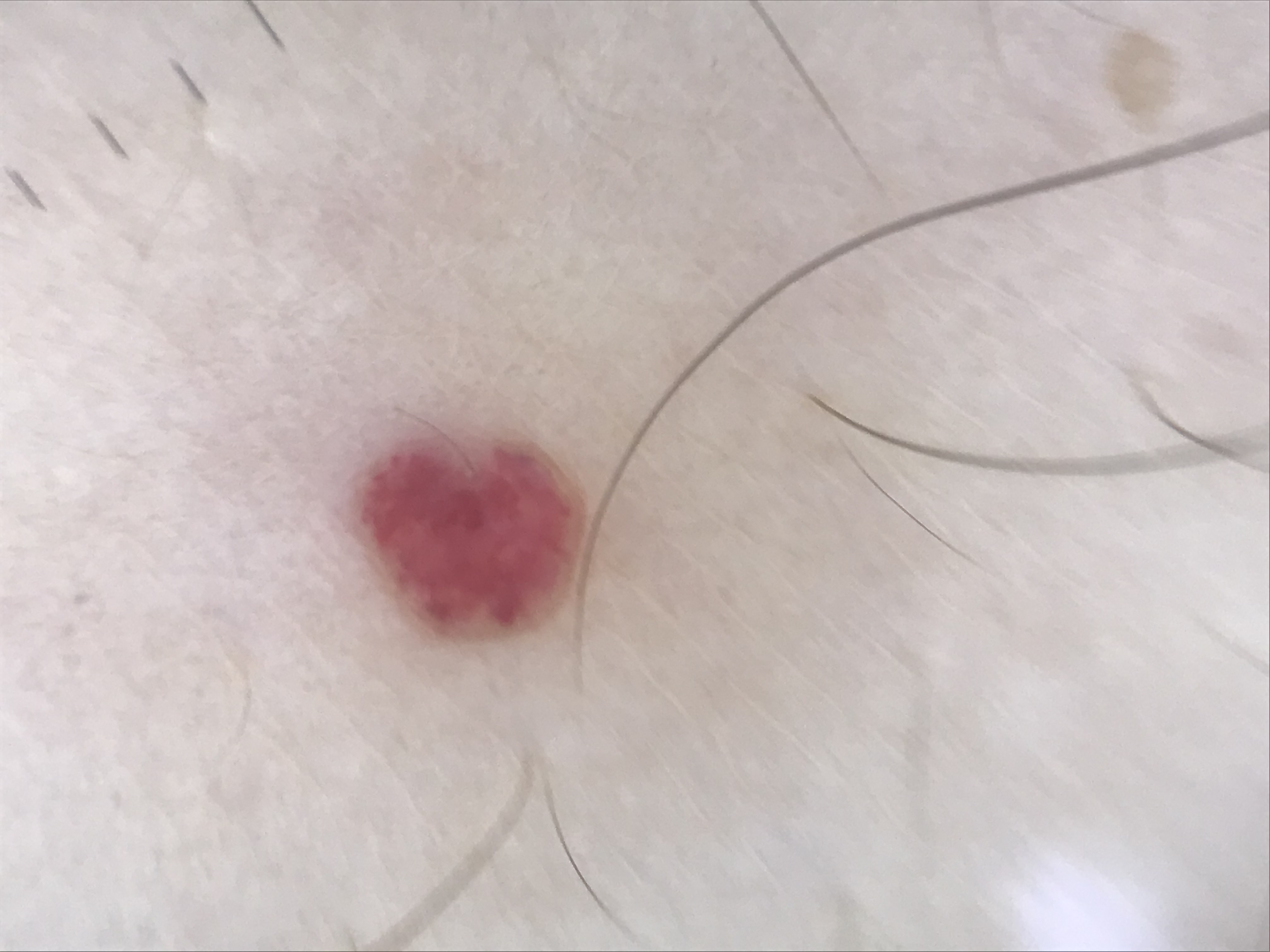– image type · dermoscopy
– lesion type · vascular
– assessment · hemangioma (expert consensus)